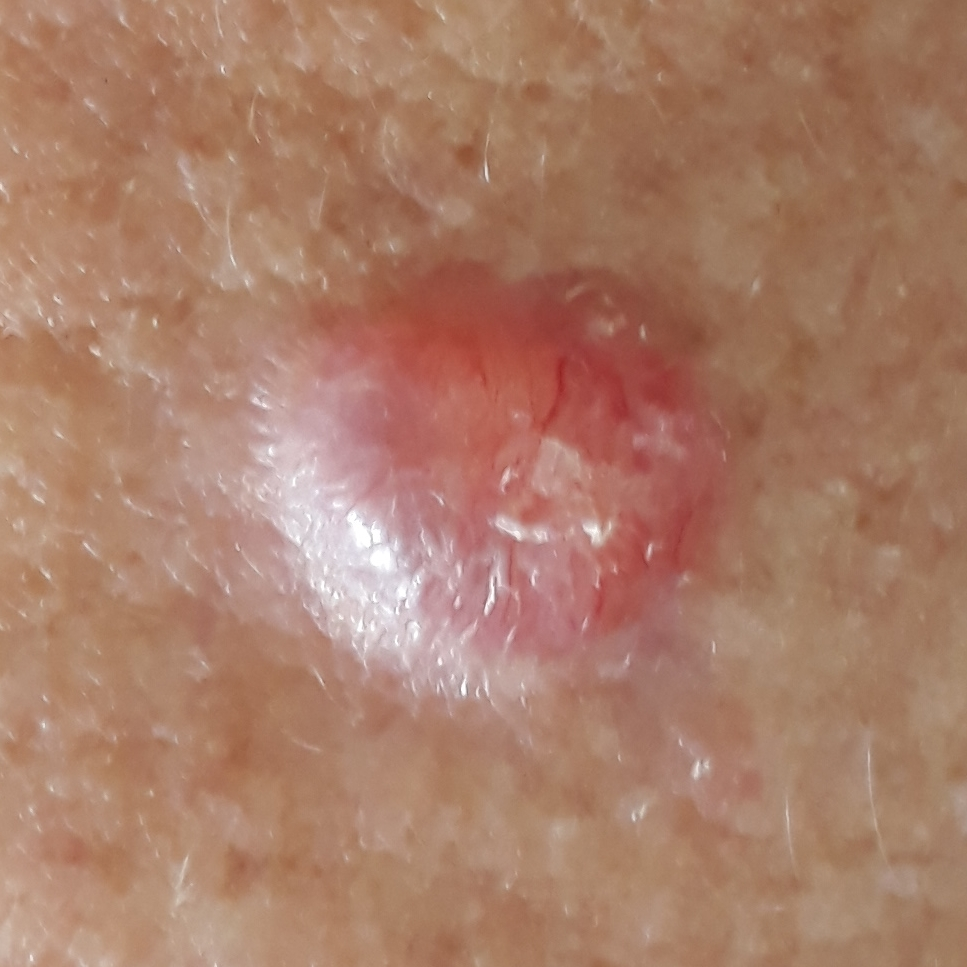Case summary:
A female patient in their early 50s. The chart records prior skin cancer (patient or family) and prior malignancy (patient or family). A clinical photograph showing a skin lesion. The lesion is on the neck. The lesion is roughly 7 by 5 mm. The patient describes that the lesion is elevated, but does not itch and does not hurt.
Conclusion:
On biopsy, the diagnosis was a malignancy — a basal cell carcinoma.